Dermoscopy of a skin lesion.
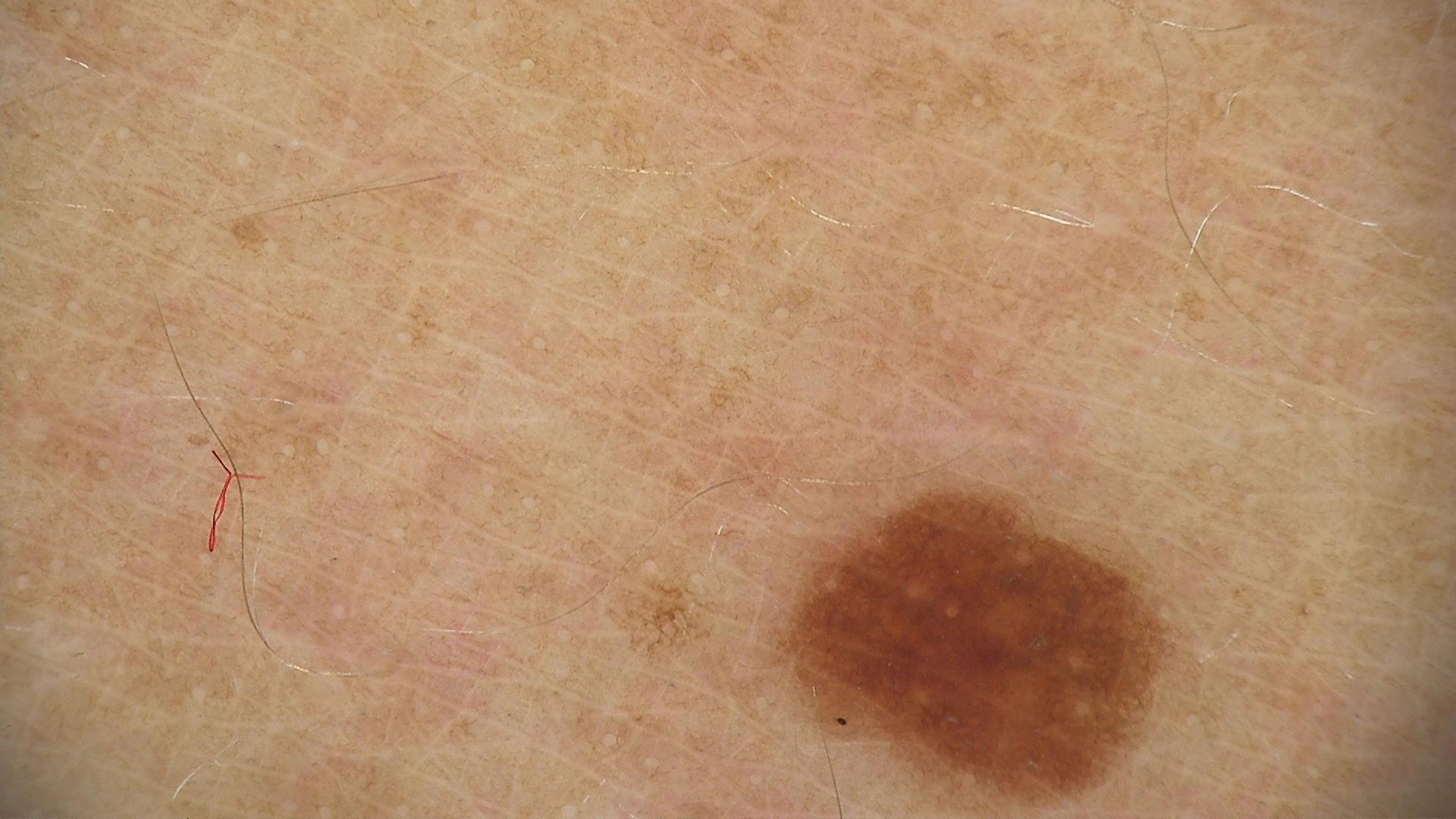diagnosis — dysplastic junctional nevus (expert consensus)